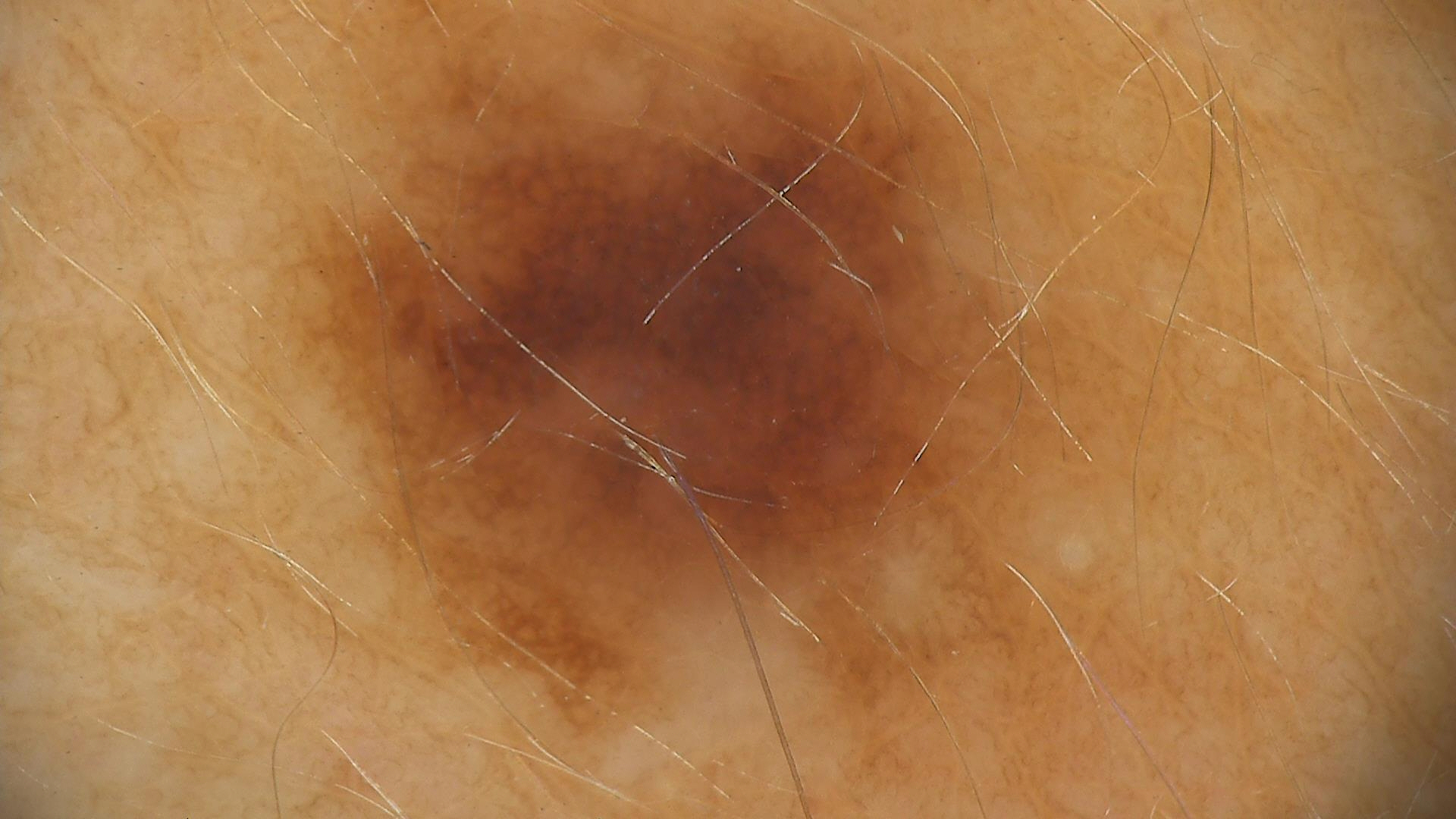modality — dermoscopy; diagnostic label — dysplastic compound nevus (expert consensus).